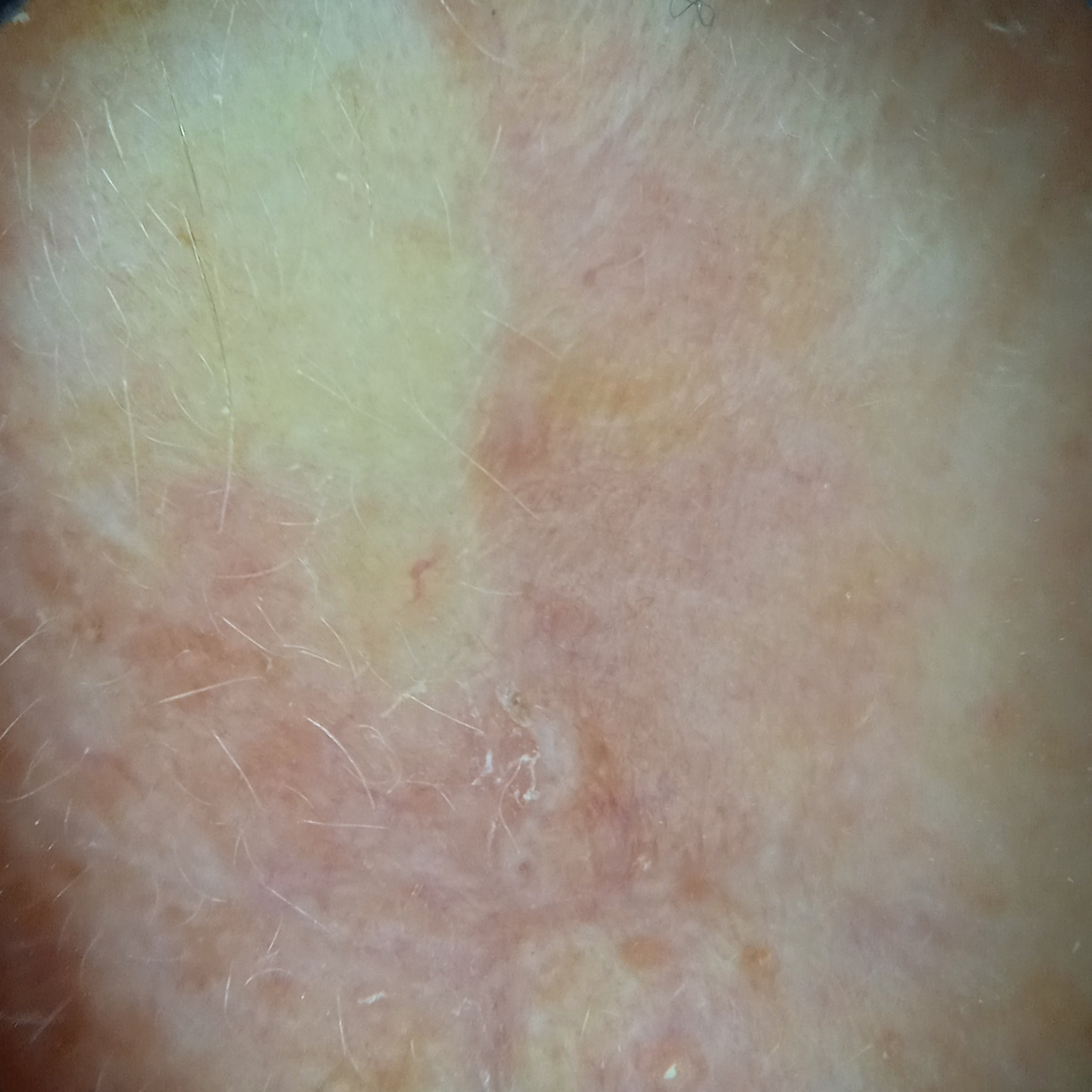Clinical context: A dermatoscopic image of a skin lesion. A female subject 68 years old. Located on the face. Conclusion: The consensus diagnosis for this lesion was an actinic keratosis.